No associated systemic symptoms reported. Located on the leg. Female contributor, age 18–29. Self-categorized by the patient as a rash. This is a close-up image. Symptoms reported: bothersome appearance and itching. The lesion is described as raised or bumpy: 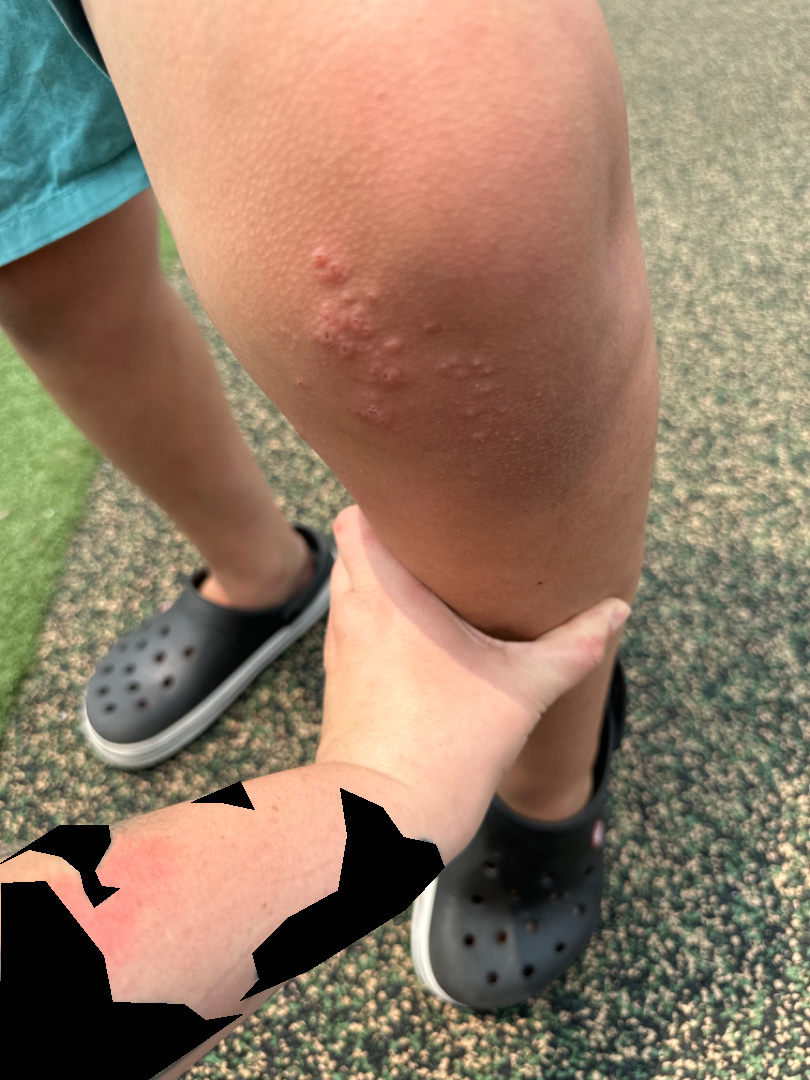The case was indeterminate on photographic review.